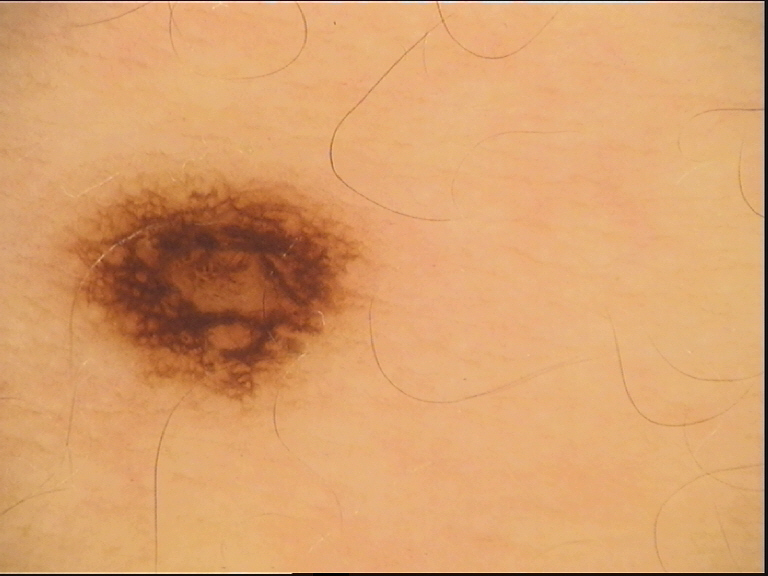diagnosis — dysplastic junctional nevus (expert consensus).